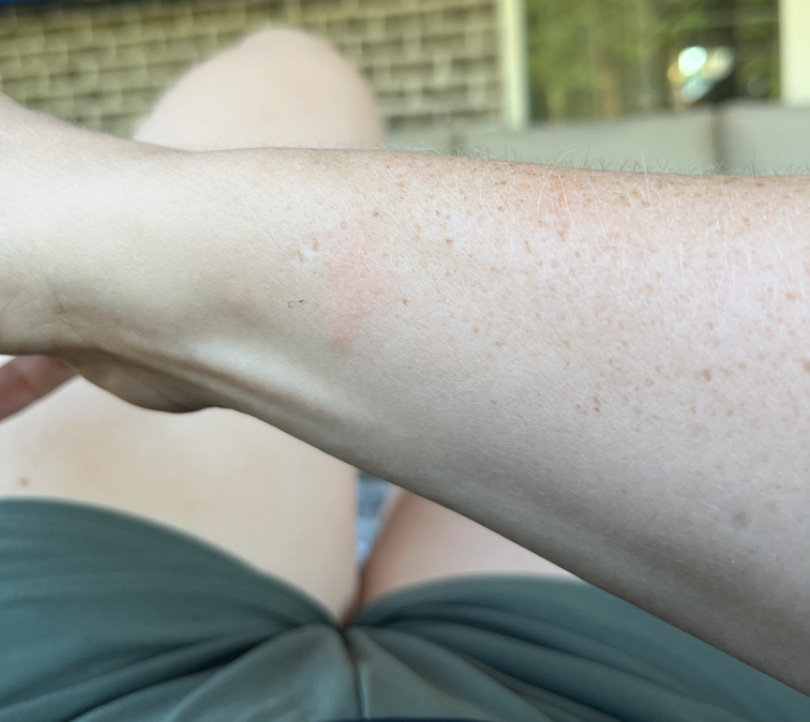Case summary:
– present for: one to four weeks
– framing: close-up
– contributor: female, age 30–39
– location: arm
– patient-reported symptoms: itching
– surface texture: raised or bumpy
– self-categorized as: a rash
– clinical impression: the differential, in no particular order, includes Eczema and Allergic Contact Dermatitis